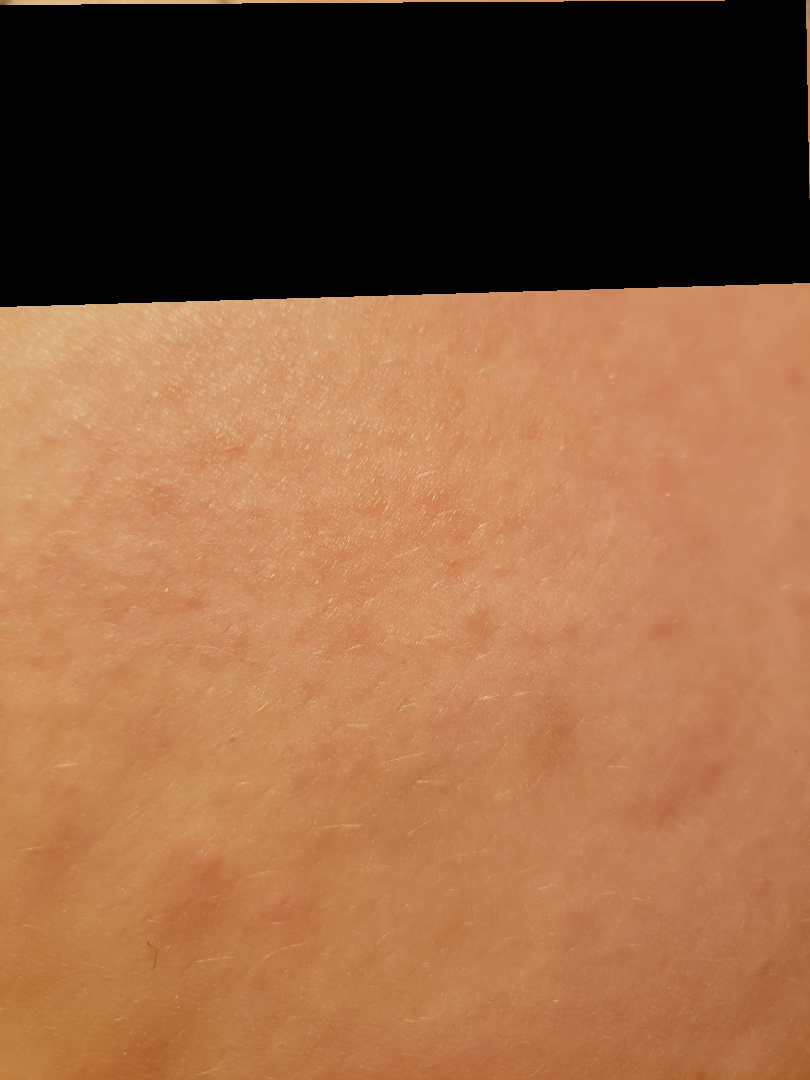On independent review by the dermatologists, Allergic Contact Dermatitis (primary); Folliculitis (possible); Urticaria (remote); Eczema (remote).